By history, prior skin cancer (patient or family), tobacco use, pesticide exposure, prior malignancy (patient or family), and alcohol use · a clinical close-up photograph of a skin lesion · a male patient in their mid-60s · Fitzpatrick skin type III:
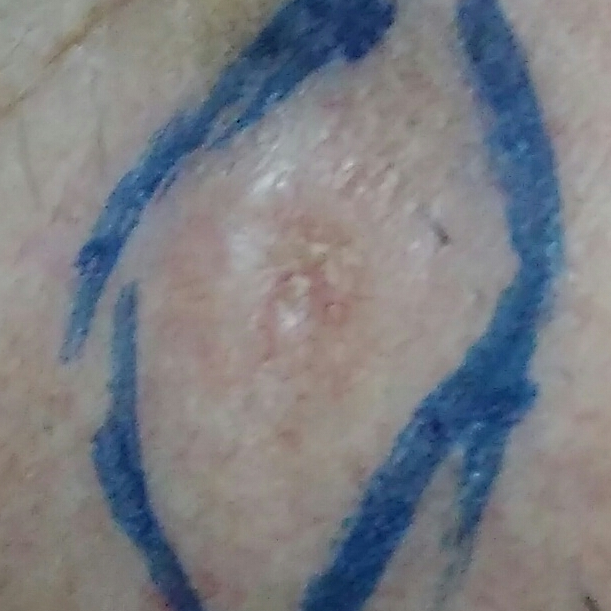Per patient report, the lesion is elevated and has grown.
Histopathological examination showed a basal cell carcinoma.